A dermatoscopic image of a skin lesion:
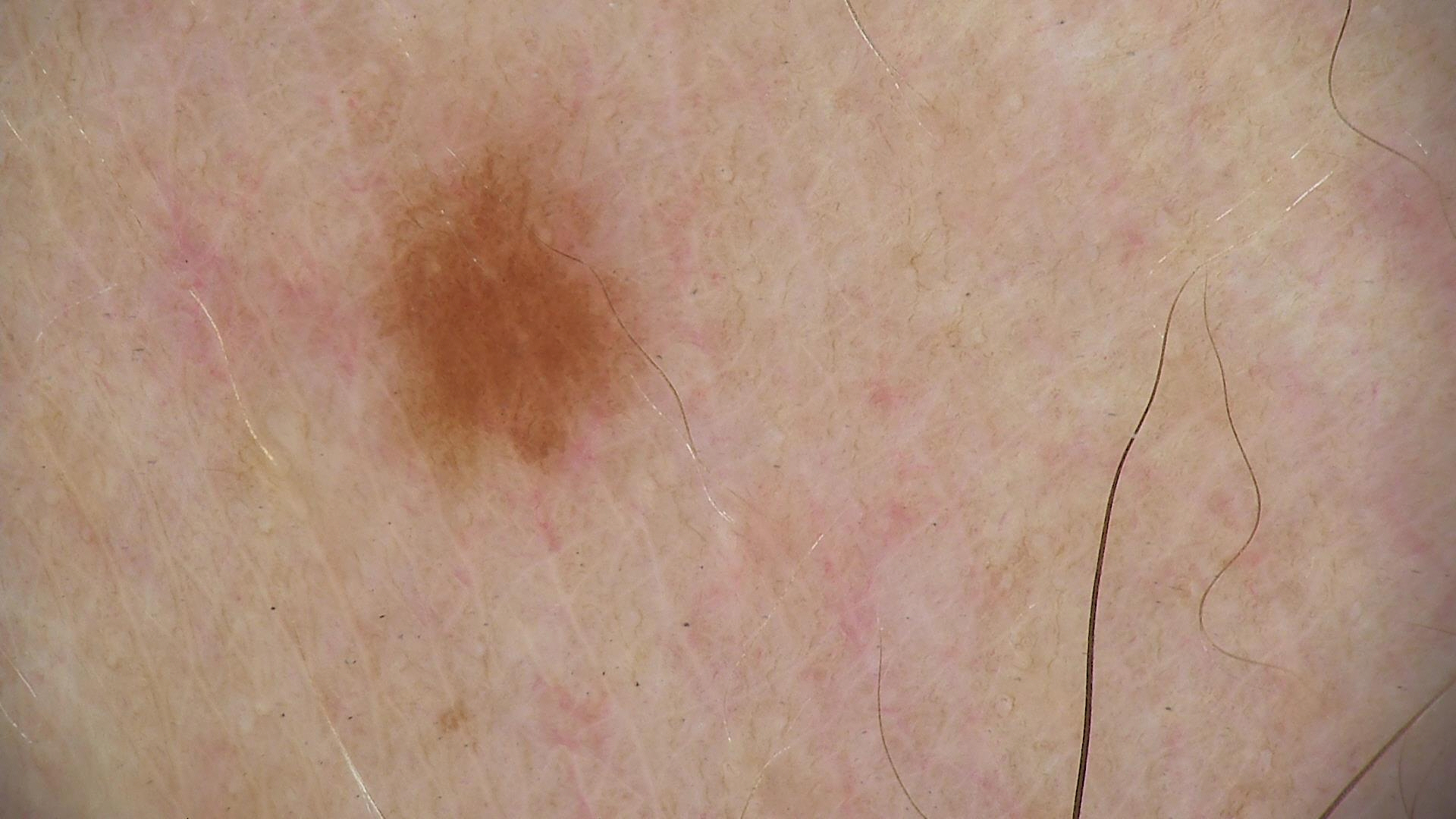Conclusion:
The diagnostic label was a dysplastic junctional nevus.